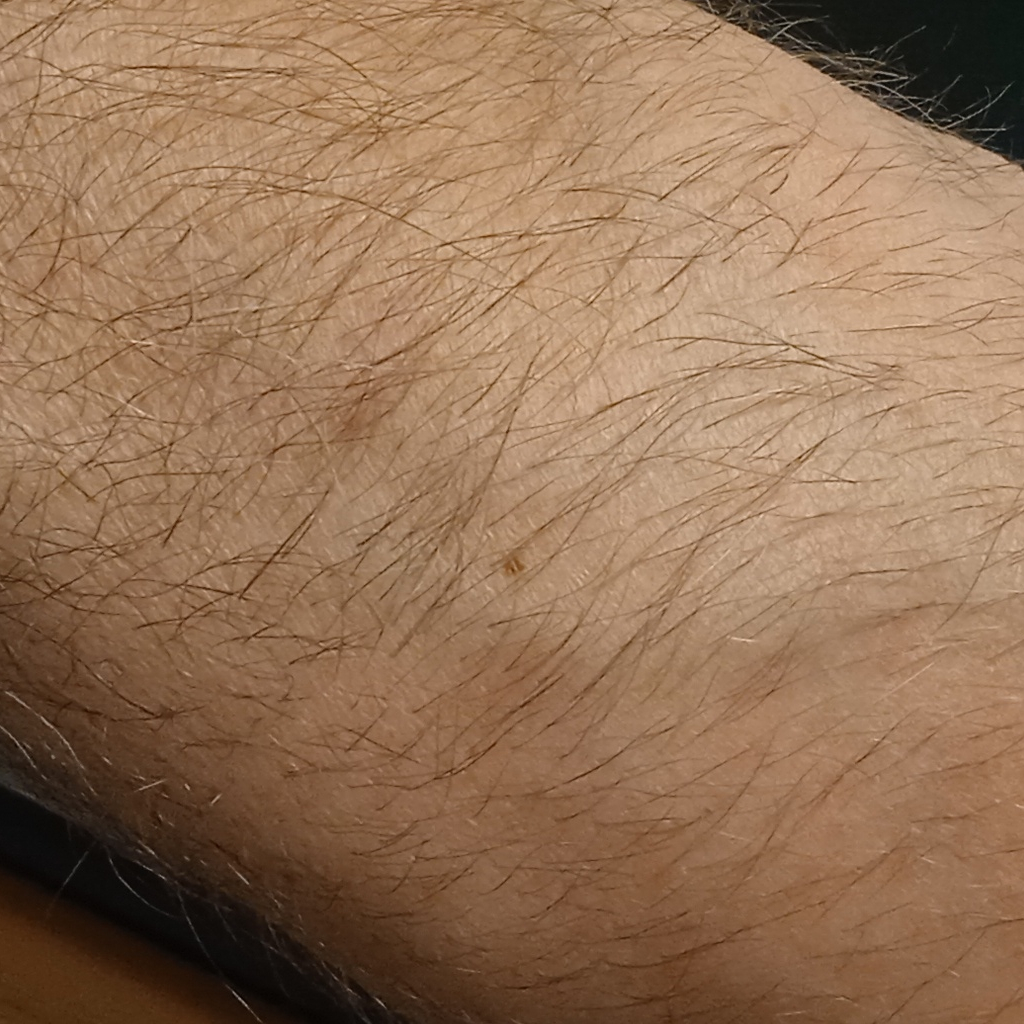{"sun_reaction": "skin reddens with sun exposure", "referral": "research study (no referral diagnosis)", "patient": {"age": 60, "sex": "male"}, "image": "clinical photo", "lesion_location": "an arm", "lesion_size": {"diameter_mm": 1.5}, "diagnosis": {"name": "melanocytic nevus", "malignancy": "benign"}}